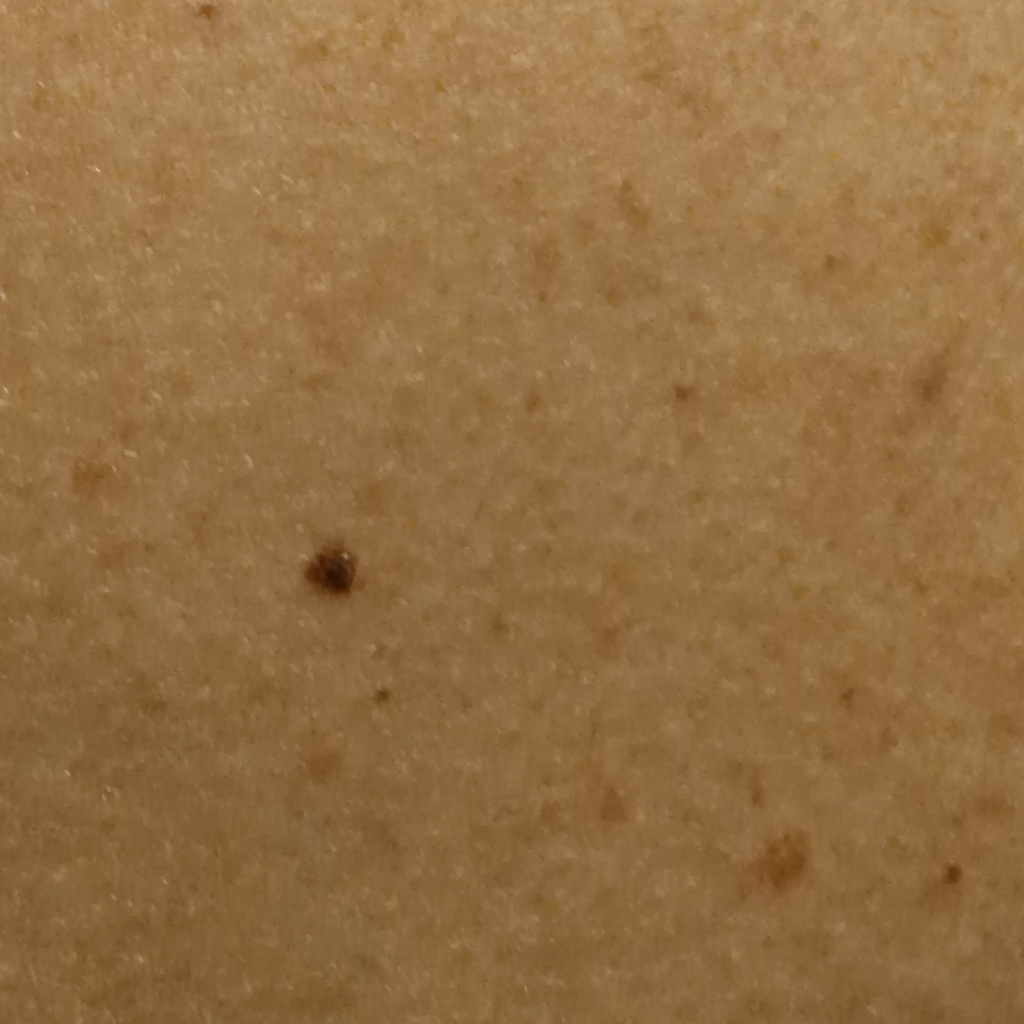Case:
• relevant history: a personal history of cancer, a family history of skin cancer
• nevus count: a moderate number of melanocytic nevi
• sun reaction: skin tans without first burning
• modality: clinical photograph
• subject: female, aged 64
• referral context: clinical suspicion of seborrheic keratosis
• anatomic site: the back
• lesion size: 3.5 mm
• diagnosis: seborrheic keratosis (biopsy-proven)